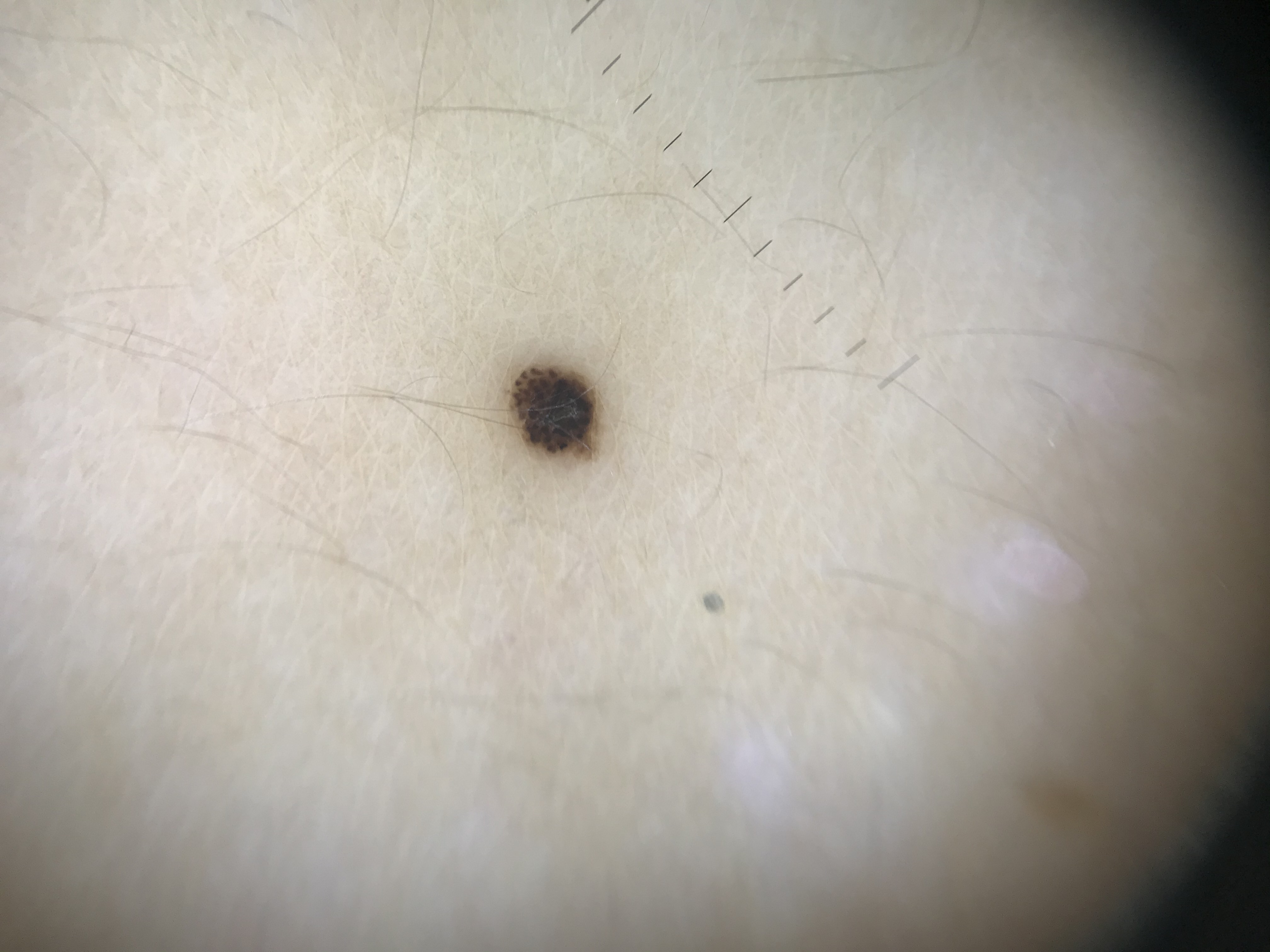Findings:
* class: junctional nevus (expert consensus)